A dermoscopic view of a skin lesion:
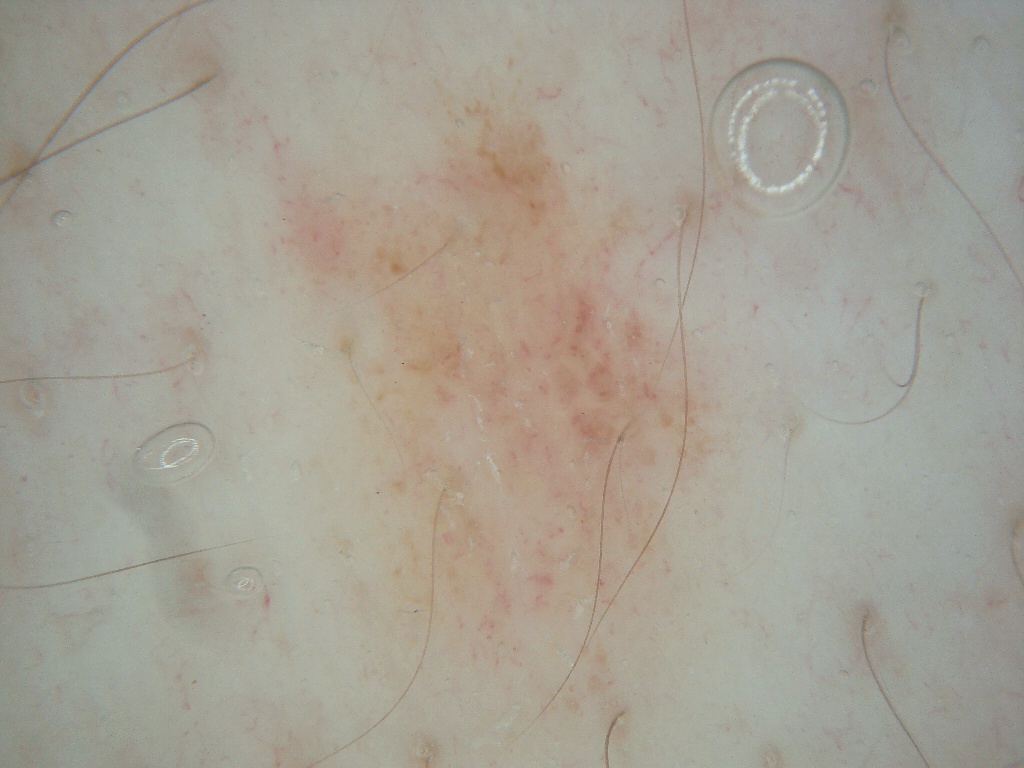Q: Where is the lesion in the image?
A: box(250, 47, 749, 751)
Q: What is the diagnosis?
A: a benign skin lesion